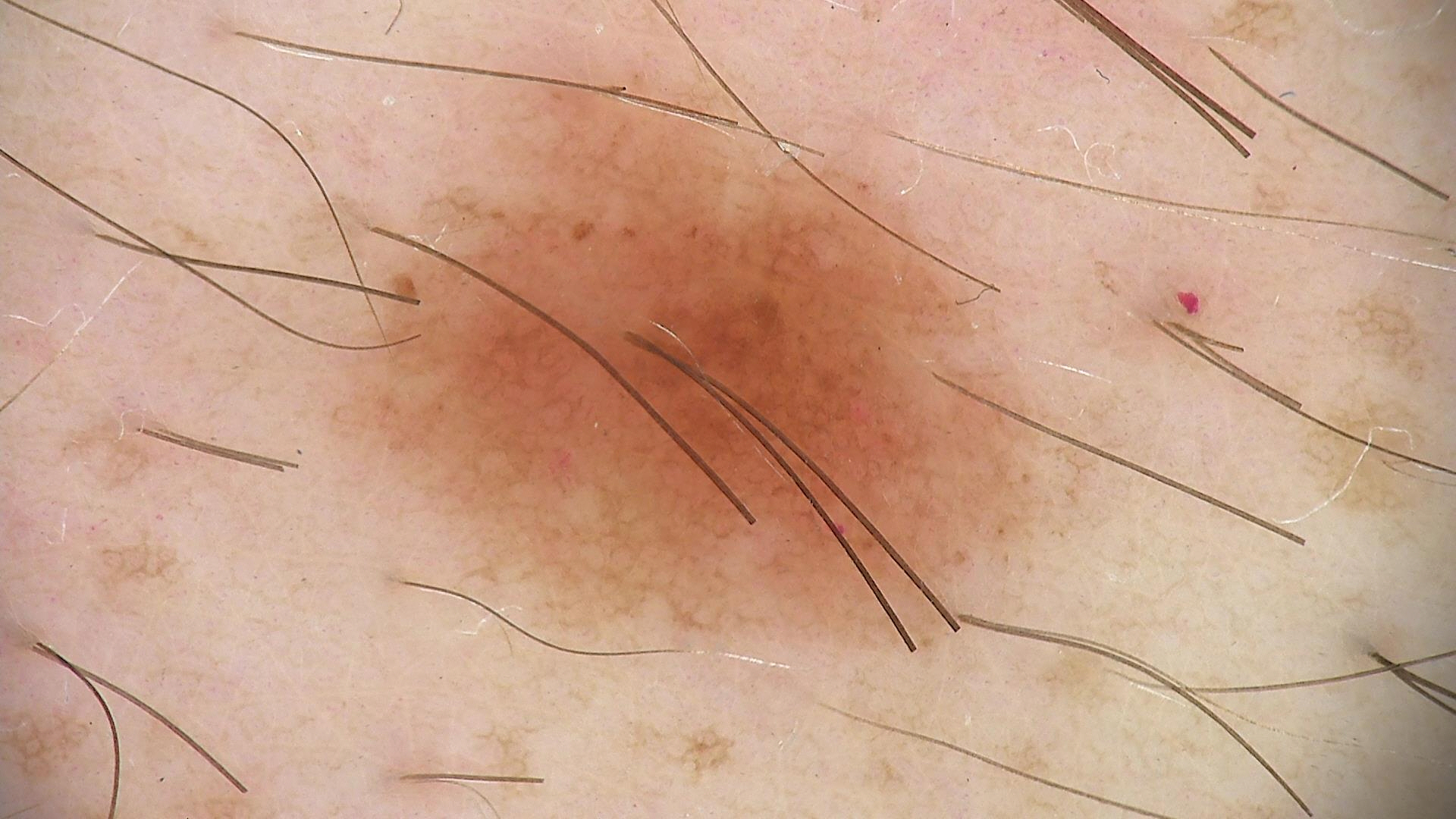| field | value |
|---|---|
| diagnostic label | dysplastic junctional nevus (expert consensus) |